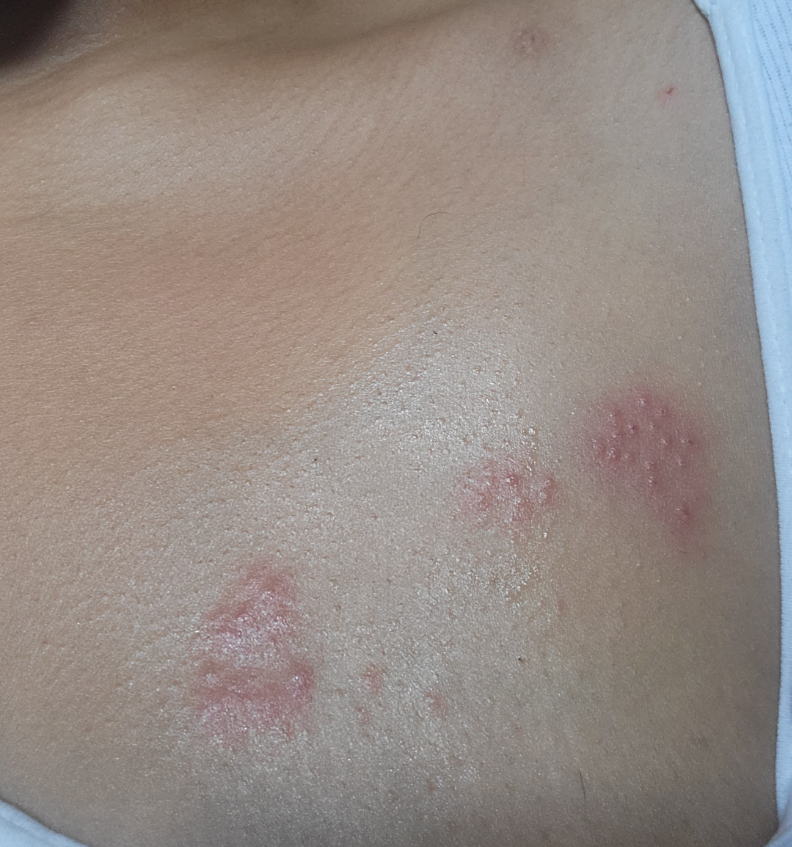Notes:
– patient's own categorization: a rash
– view: close-up
– skin tone: Fitzpatrick phototype IV; human graders estimated Monk Skin Tone 4 or 5
– lesion symptoms: burning, pain and itching
– associated systemic symptoms: fatigue, chills and joint pain
– differential: most consistent with Herpes Zoster; less probable is Contact dermatitis; a remote consideration is Allergic Contact Dermatitis; less likely is Herpes Simplex